The affected area is the arm and front of the torso · close-up view · the patient is male.
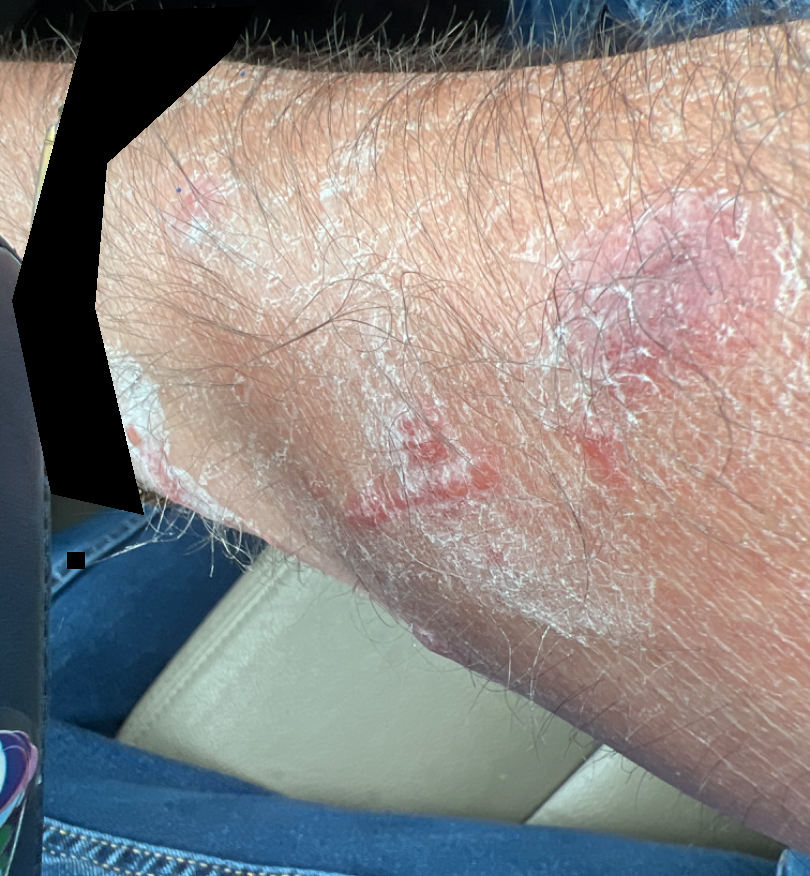patient_category: a rash
skin_tone:
  fitzpatrick: II
  monk_skin_tone:
    - 3
    - 4
texture: fluid-filled
symptoms: itching
duration: less than one week
differential:
  tied_lead:
    - Allergic Contact Dermatitis
    - Contact dermatitis